A dermoscopic image of a skin lesion:
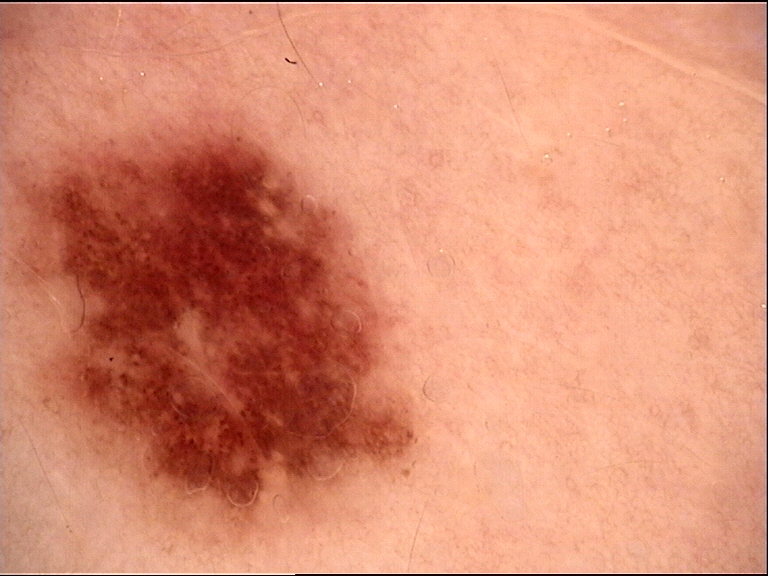Findings:
- assessment — dysplastic junctional nevus (expert consensus)